A dermatoscopic image of a skin lesion.
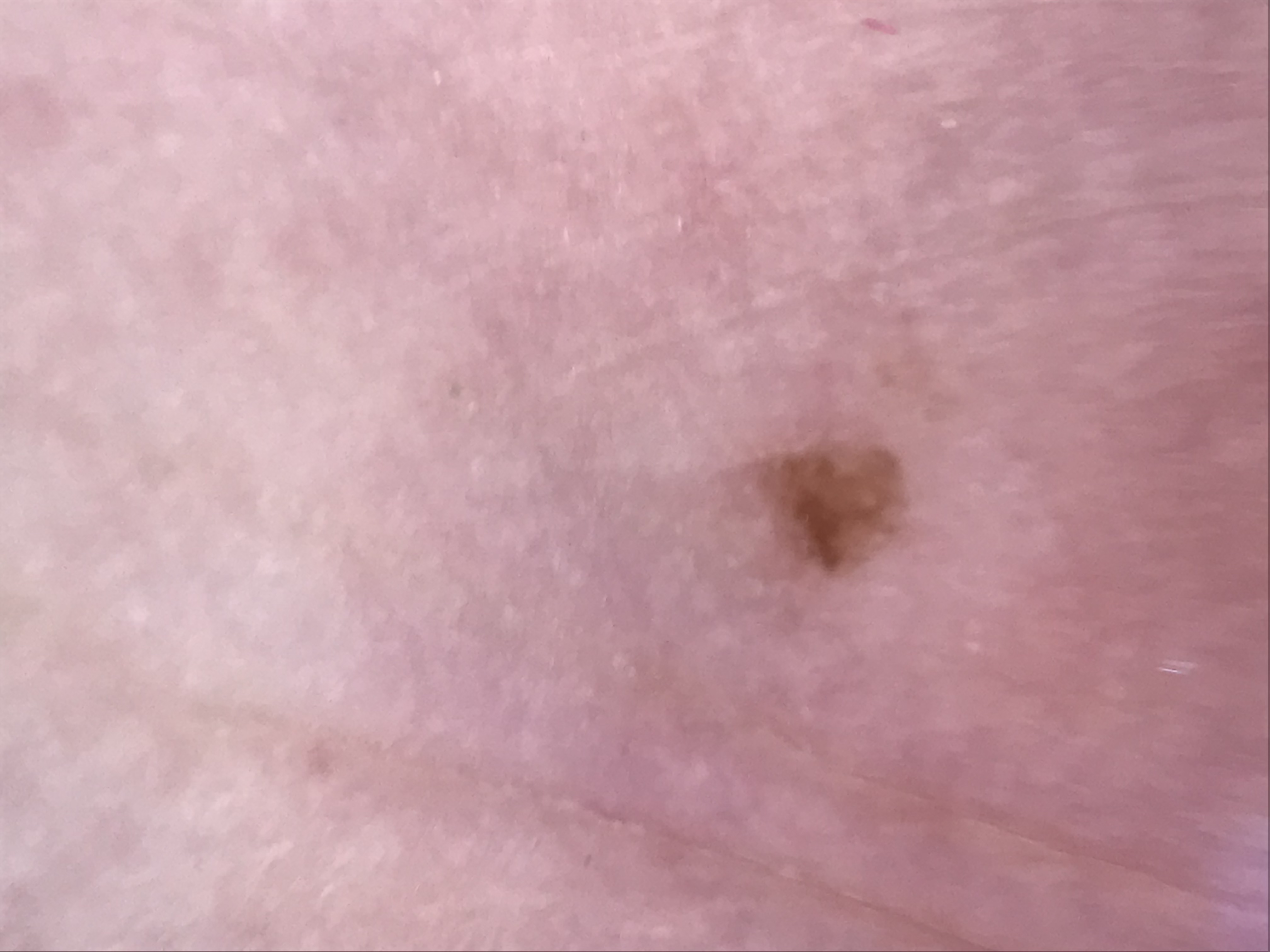Q: What is the diagnosis?
A: acral junctional nevus (expert consensus)